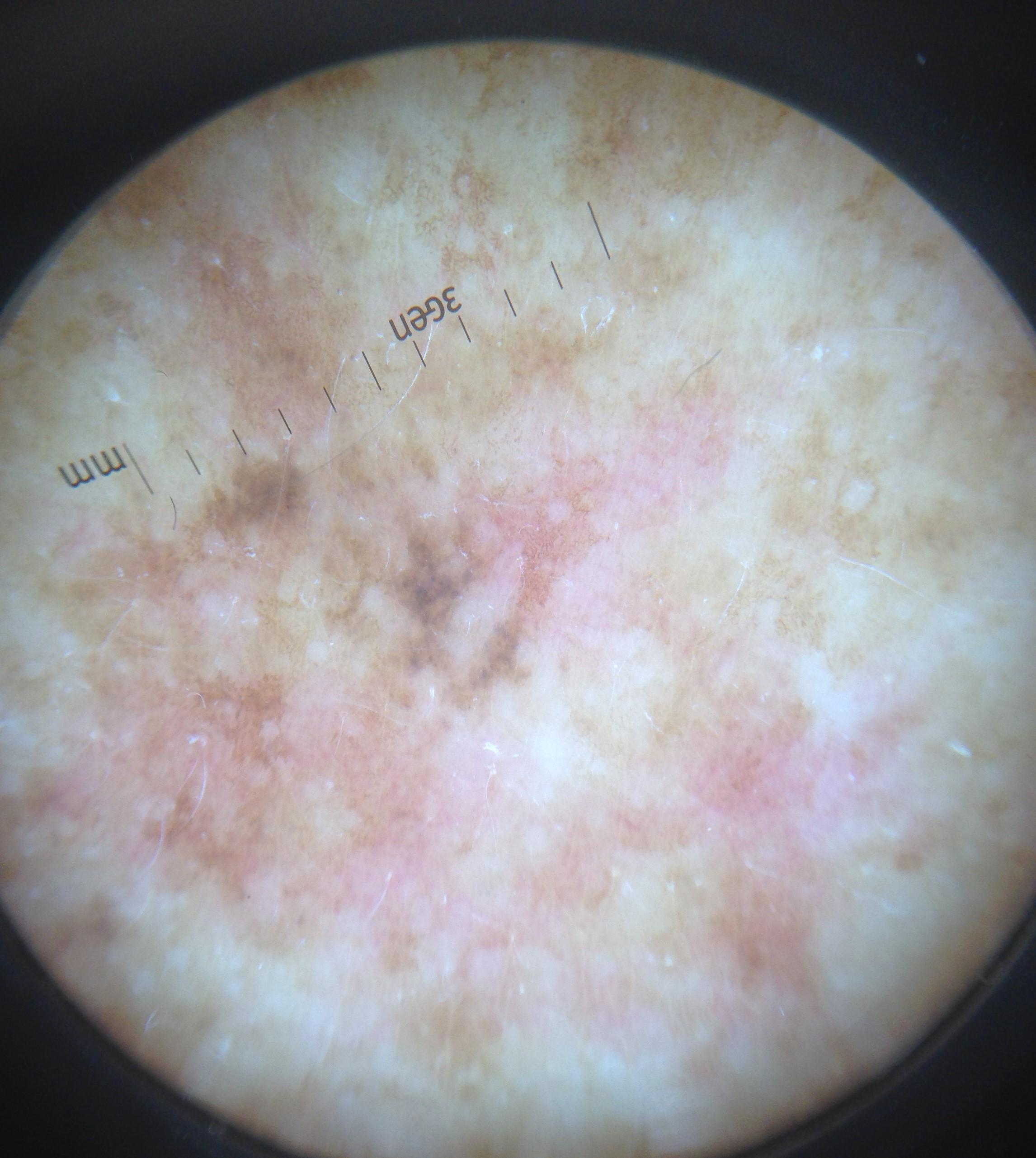Summary: A dermoscopic photograph of a skin lesion. Impression: The diagnosis was a premalignant, keratinocytic lesion — an actinic keratosis.